The lesion involves the leg, a close-up photograph:
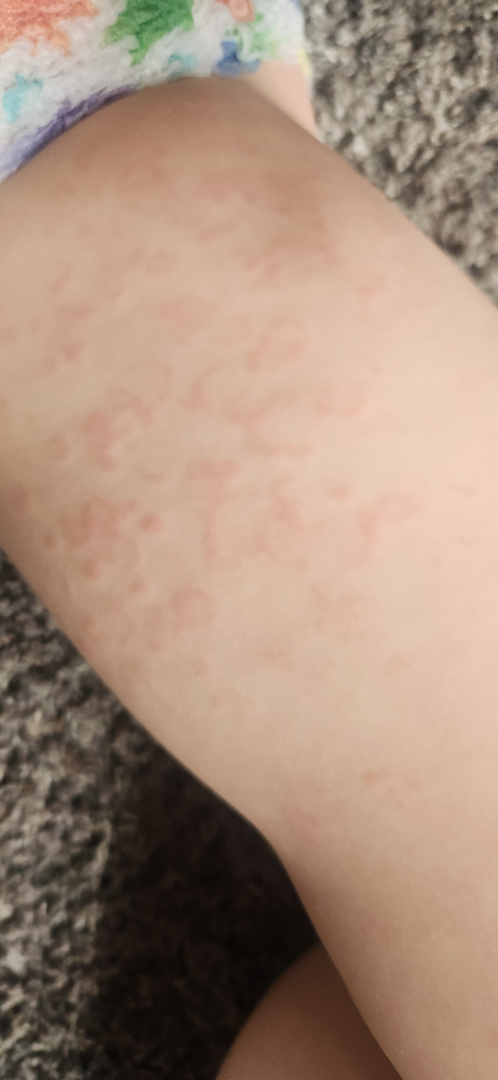differential diagnosis = Urticaria (primary); Insect Bite (considered); Allergic Contact Dermatitis (considered).